This is a close-up image. The affected area is the leg, head or neck and arm:
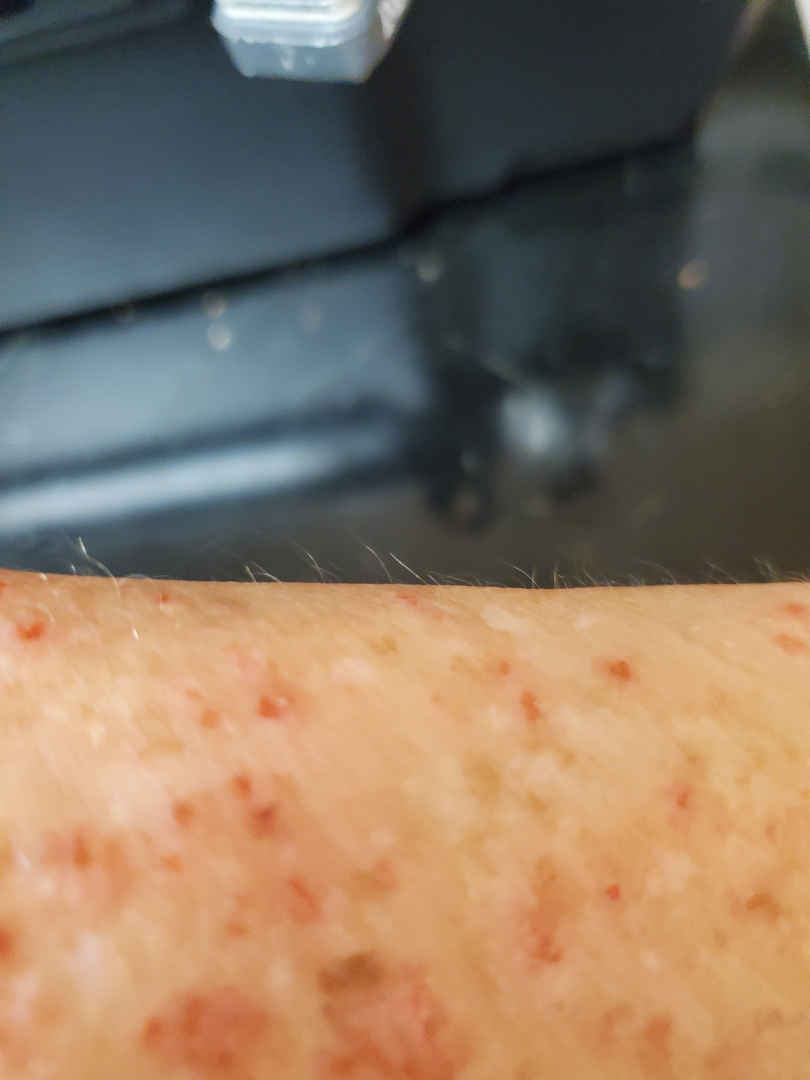Findings:
– assessment · could not be assessed
– skin tone · lay reviewers estimated MST 2 or 3
– self-categorized as · a rash
– associated systemic symptoms · none reported
– surface texture · raised or bumpy
– patient-reported symptoms · bothersome appearance, itching and pain
– symptom duration · less than one week